The subject is a male aged 58 to 62; a dermoscopic image of a skin lesion — 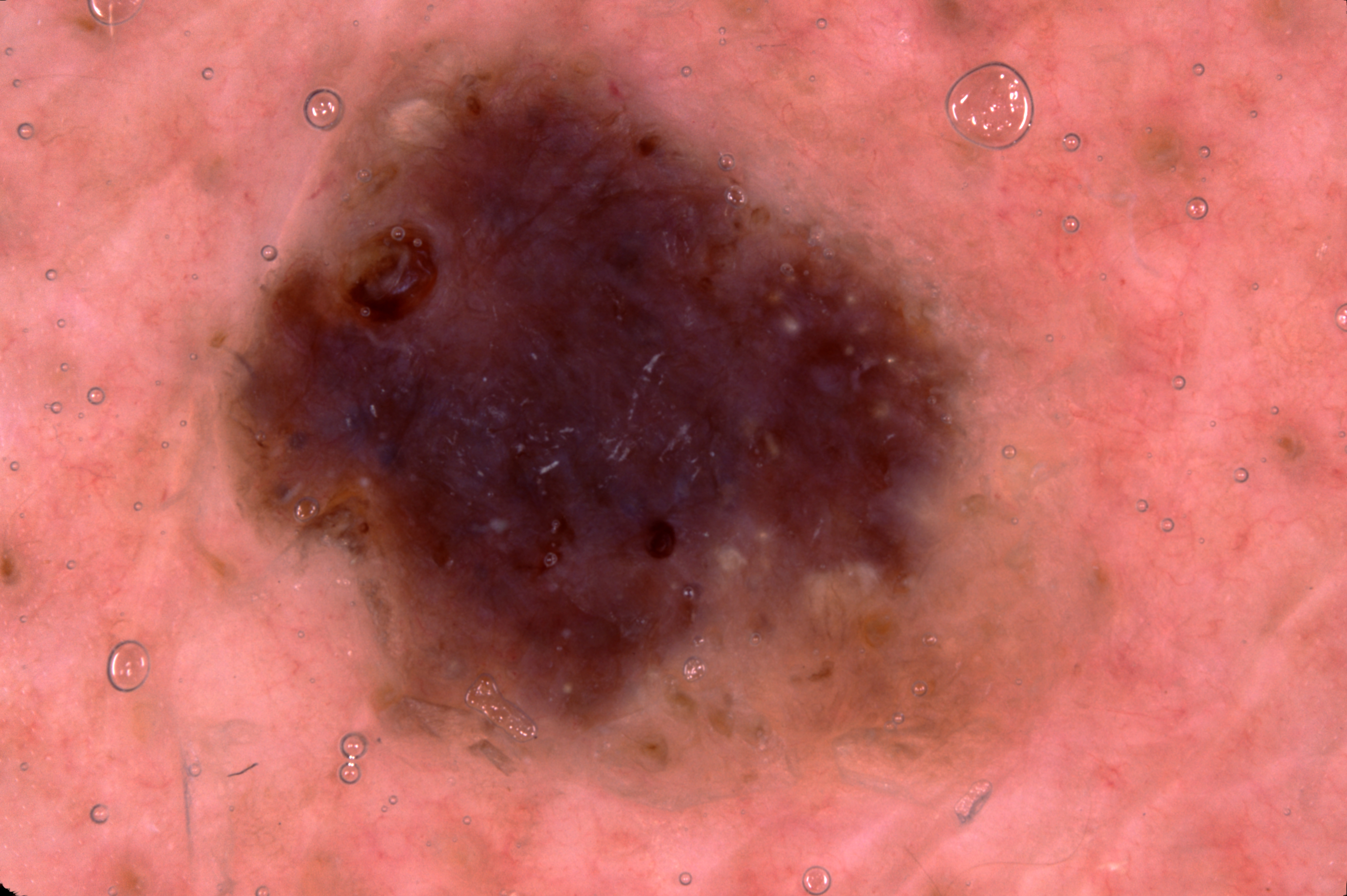Dermoscopy demonstrates milia-like cysts. As (left, top, right, bottom), the lesion occupies the region 232/56/958/728. The lesion covers approximately 28% of the dermoscopic field. The clinical diagnosis was a seborrheic keratosis, a keratinocytic lesion.